A close-up photograph, the lesion involves the back of the torso: 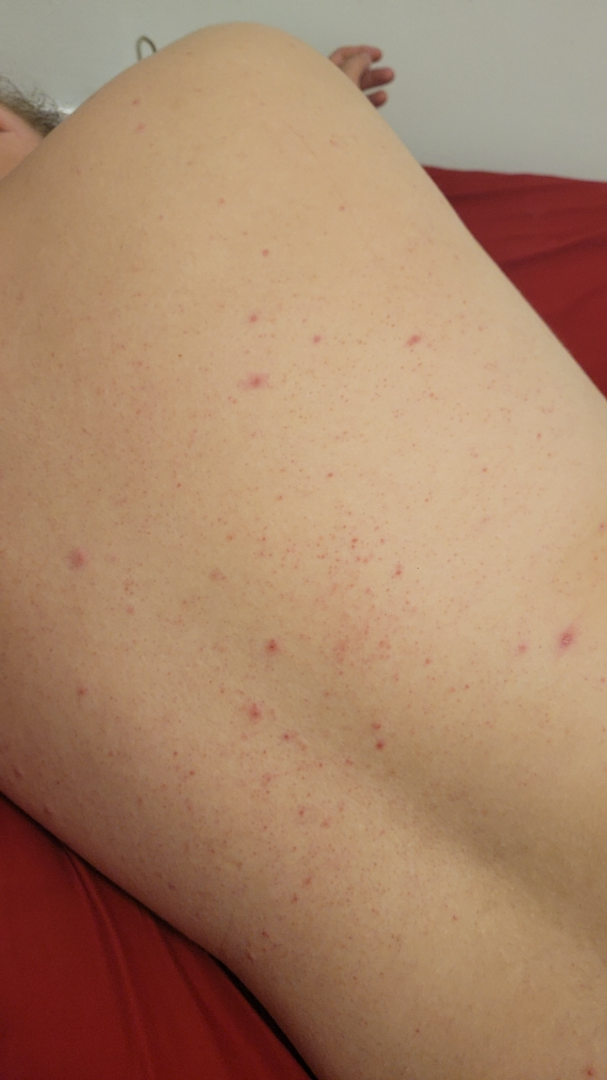dermatologist impression = a single dermatologist reviewed the case: most likely Folliculitis; also consider Acne.